The photograph was taken at an angle; located on the leg: 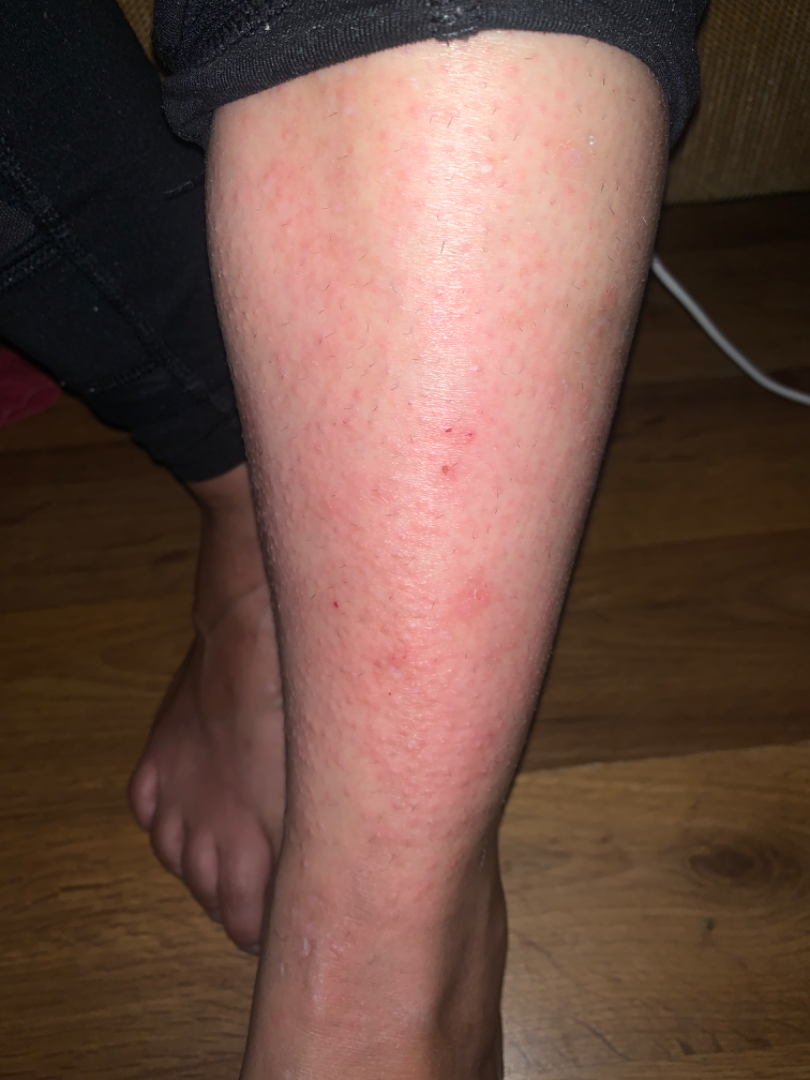The patient described the issue as a rash.
Most likely Eczema; also consider Allergic Contact Dermatitis.